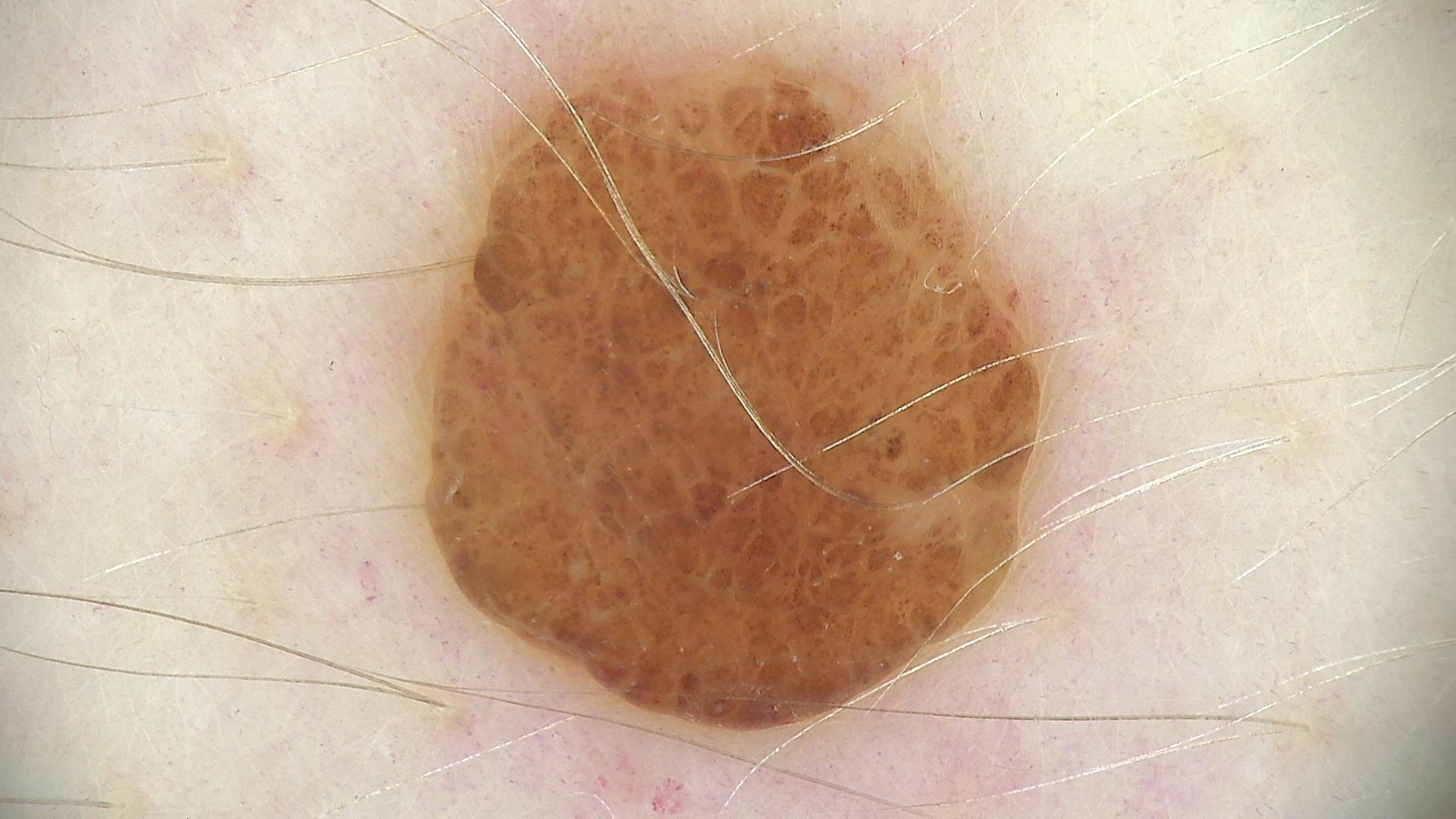Q: What kind of image is this?
A: dermoscopy
Q: What is the diagnosis?
A: compound nevus (expert consensus)